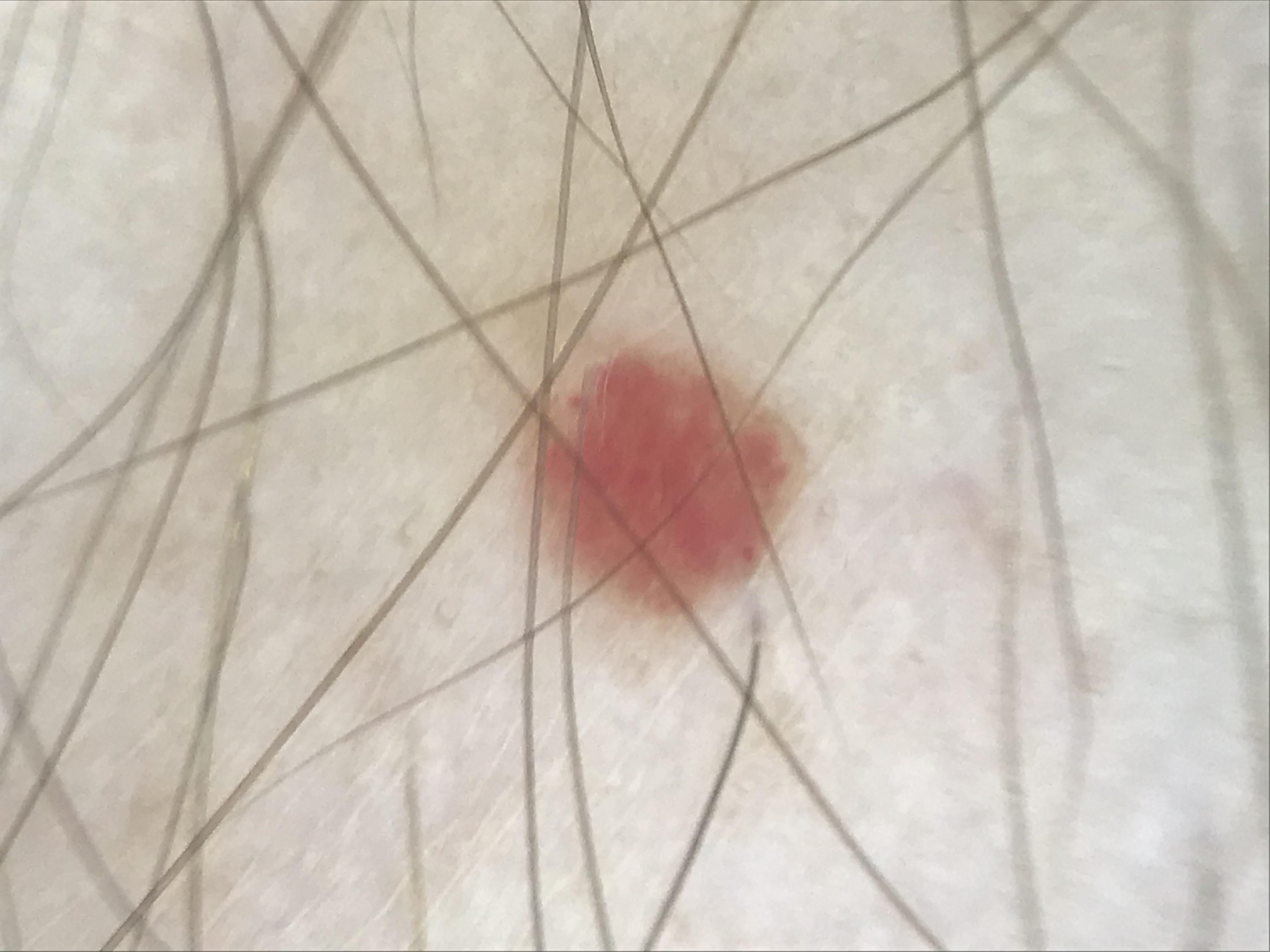Impression:
Classified as a vascular, benign lesion — a hemangioma.